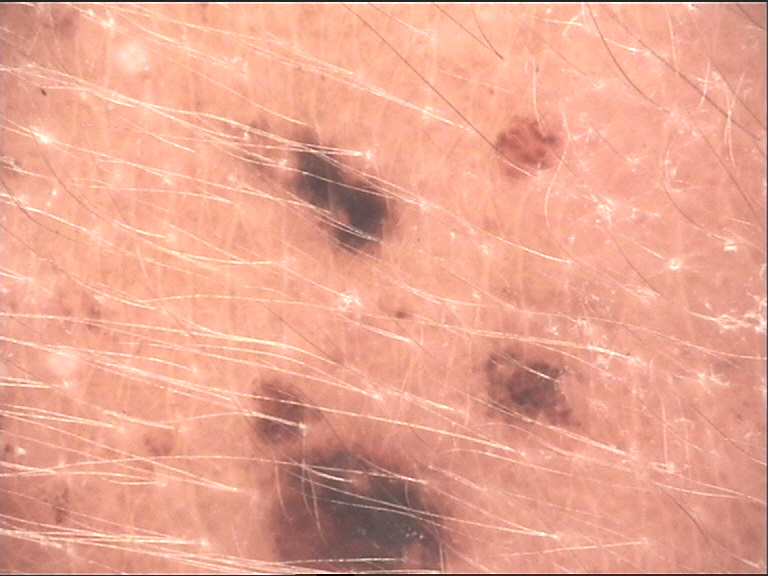image=dermatoscopy | subtype=banal | class=congenital compound nevus (expert consensus).